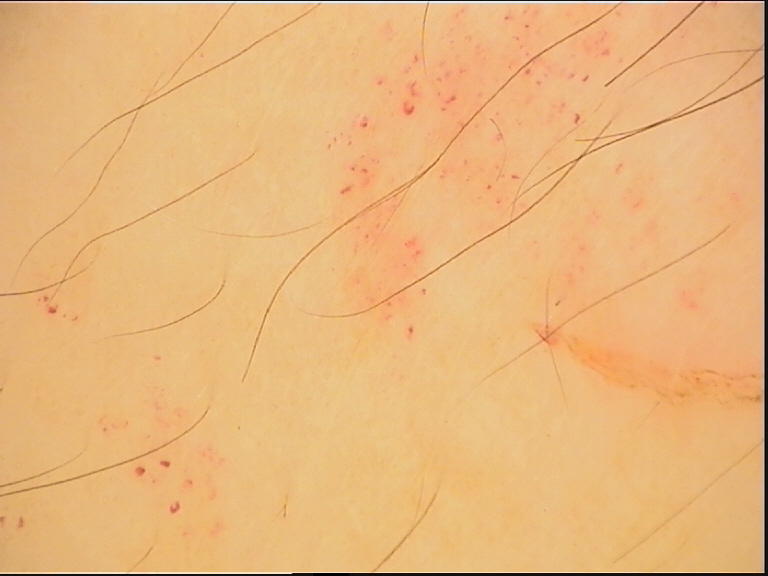Dermoscopy of a skin lesion. The architecture is that of a vascular lesion. Classified as a hemangioma.